A dermoscopy image of a single skin lesion.
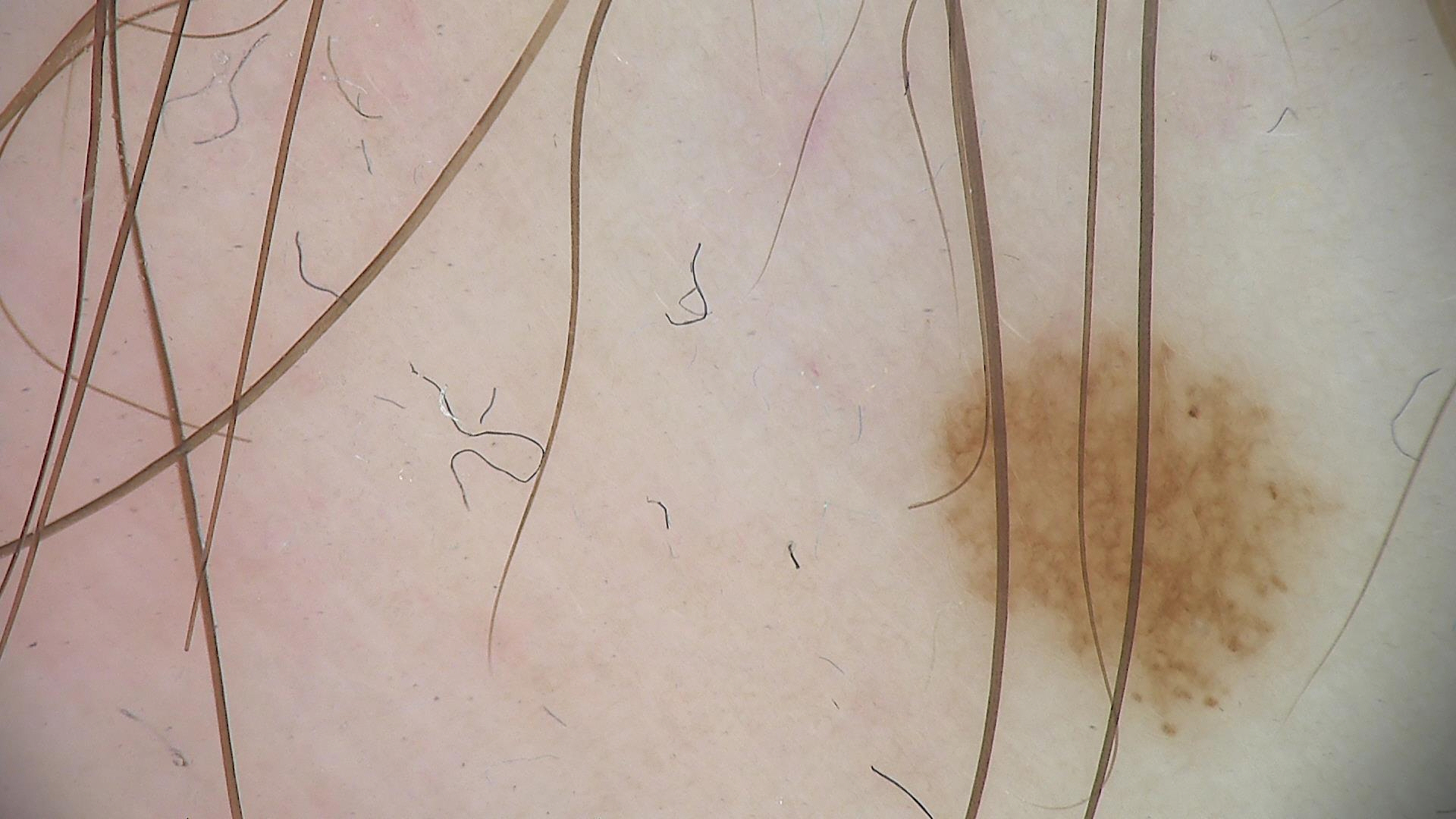Q: What is this lesion?
A: dysplastic junctional nevus (expert consensus)